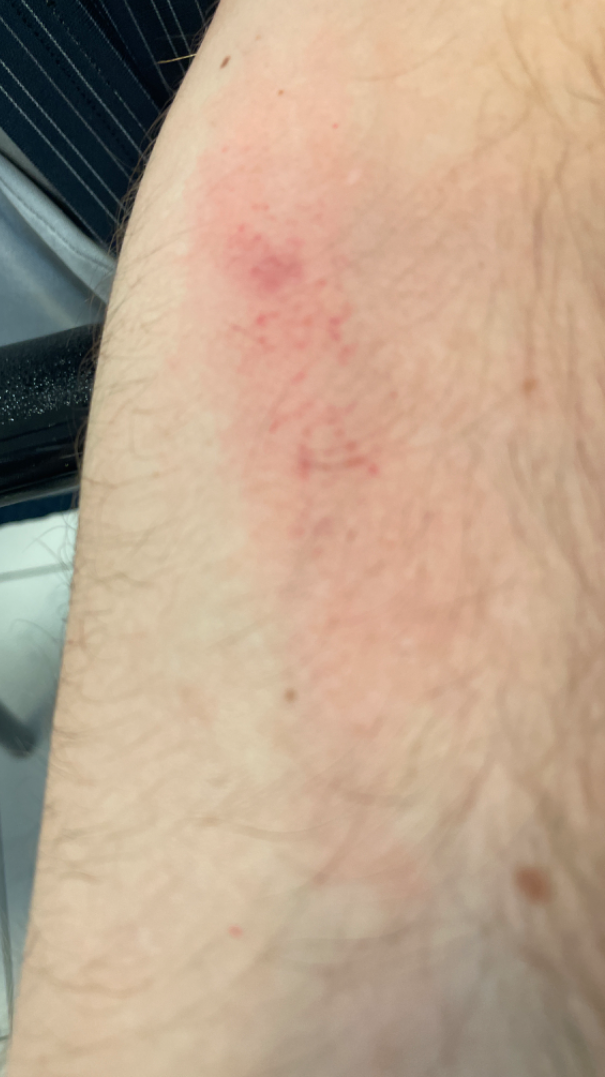Findings:
The image was not sufficient for the reviewer to characterize the skin condition.